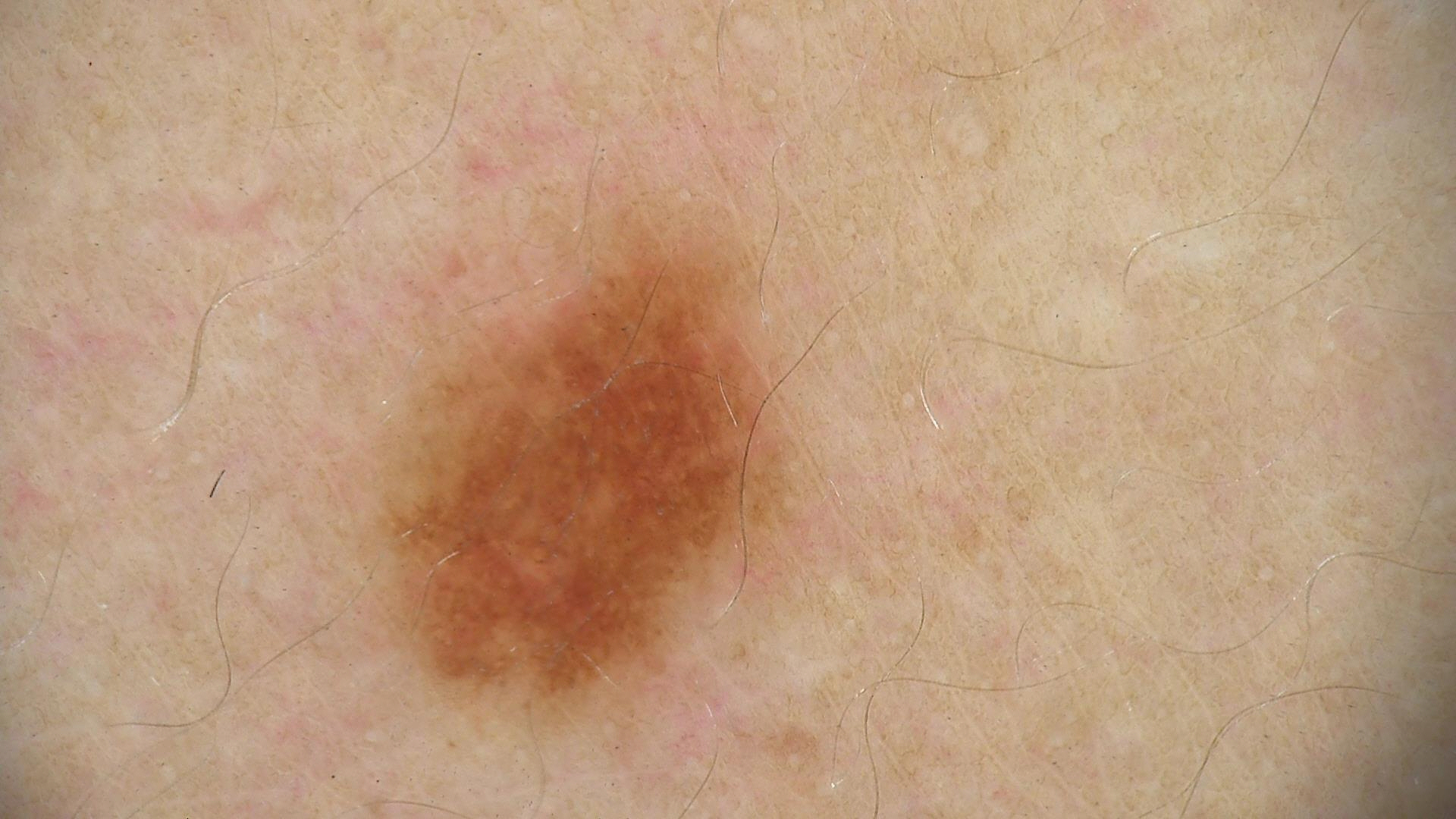Classified as a dysplastic junctional nevus.